A clinical overview photograph of a skin lesion · the chart records a prior melanoma · a female patient approximately 60 years of age · the patient is Fitzpatrick II: 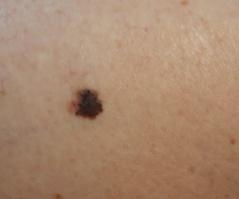pathology — Melanoma (biopsy-proven).